A dermoscopic photograph of a skin lesion:
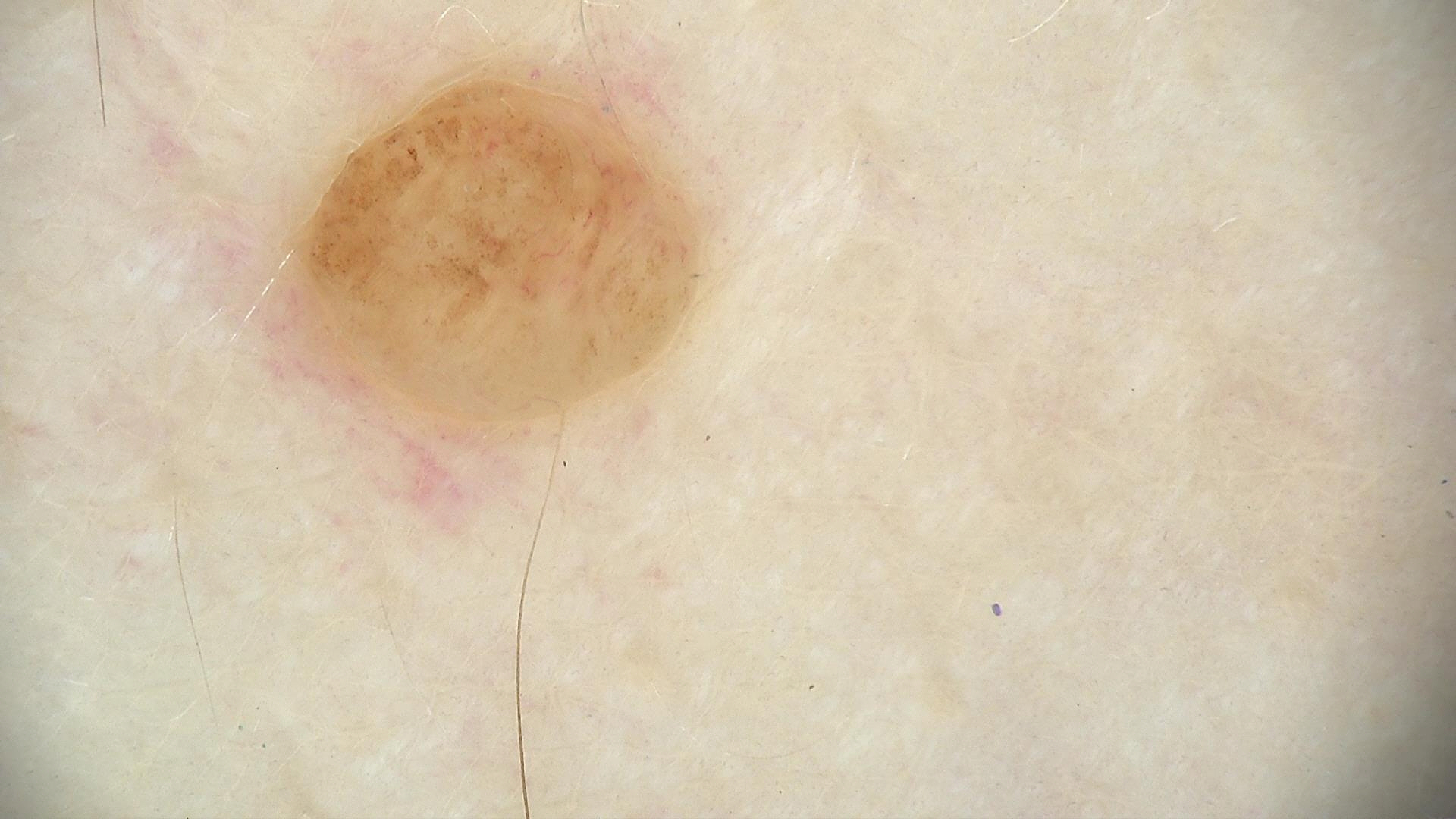Conclusion: The diagnostic label was a banal lesion — a dermal nevus.